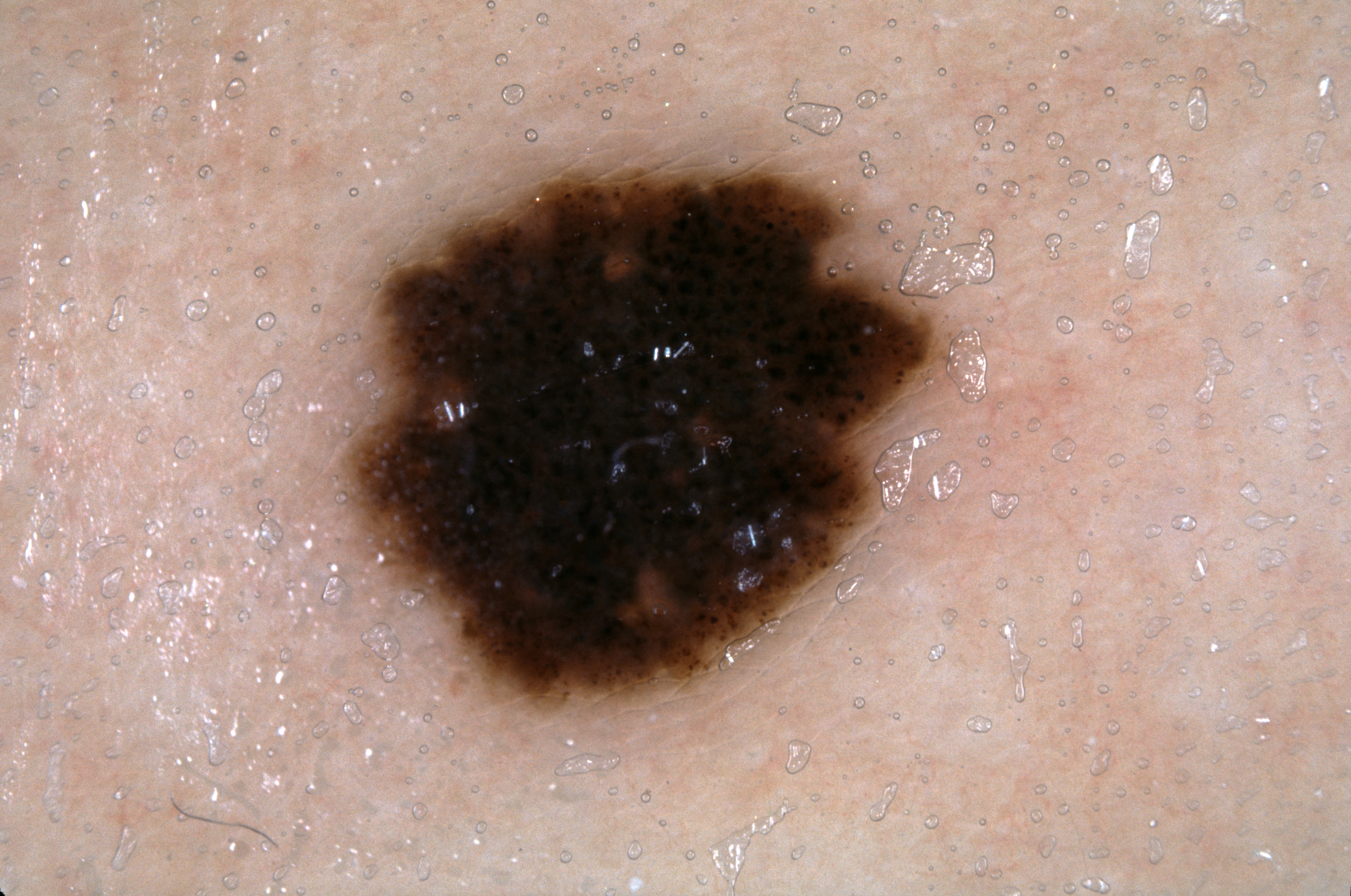image type = dermoscopy of a skin lesion; bounding box = <bbox>350, 165, 932, 705</bbox>; diagnostic label = a melanocytic nevus.